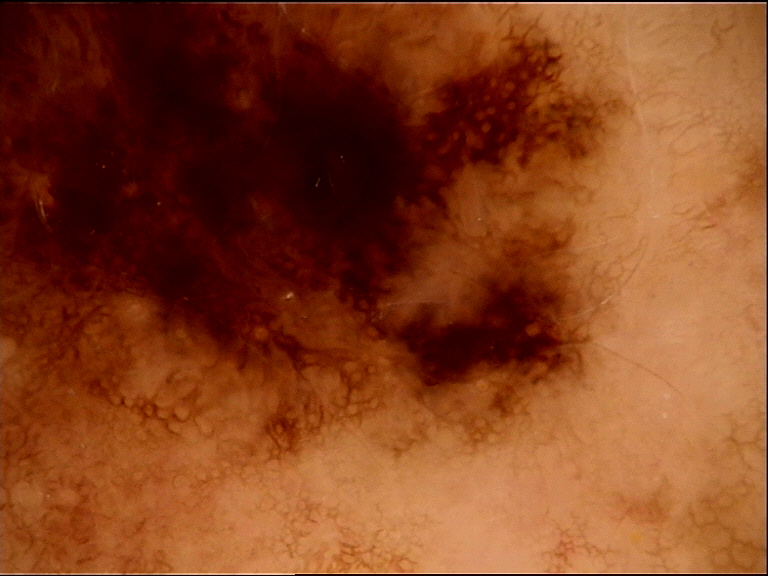A dermoscopic close-up of a skin lesion. Histopathology confirmed a melanoma.